A dermoscopy image of a single skin lesion, the subject is a male aged around 65 — 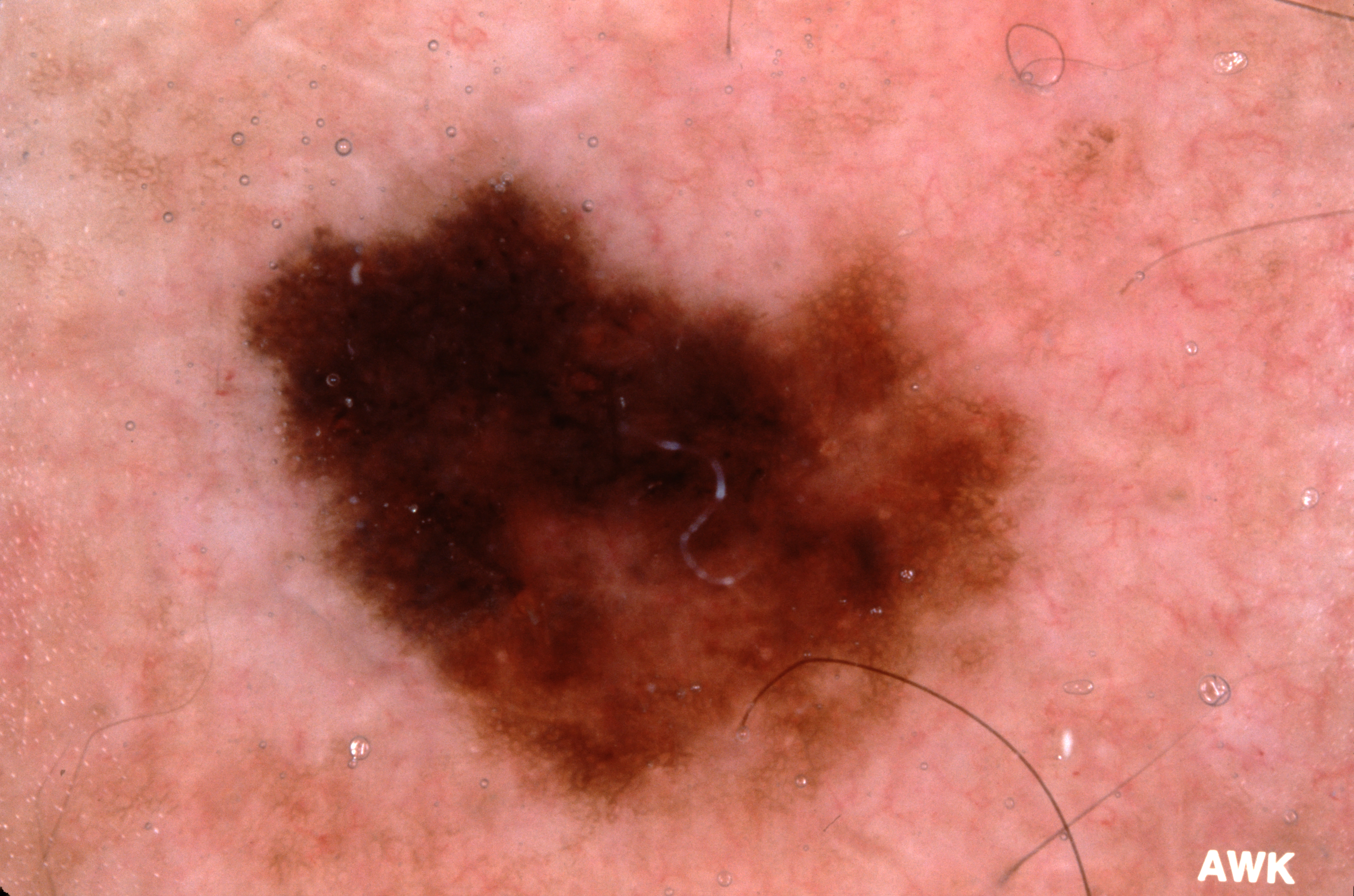Case summary:
Dermoscopic review identifies pigment network. The lesion occupies the region 235, 143, 1039, 823.
Diagnosis:
Histopathologically confirmed as a melanoma, a malignant lesion.